A dermoscopy image of a single skin lesion.
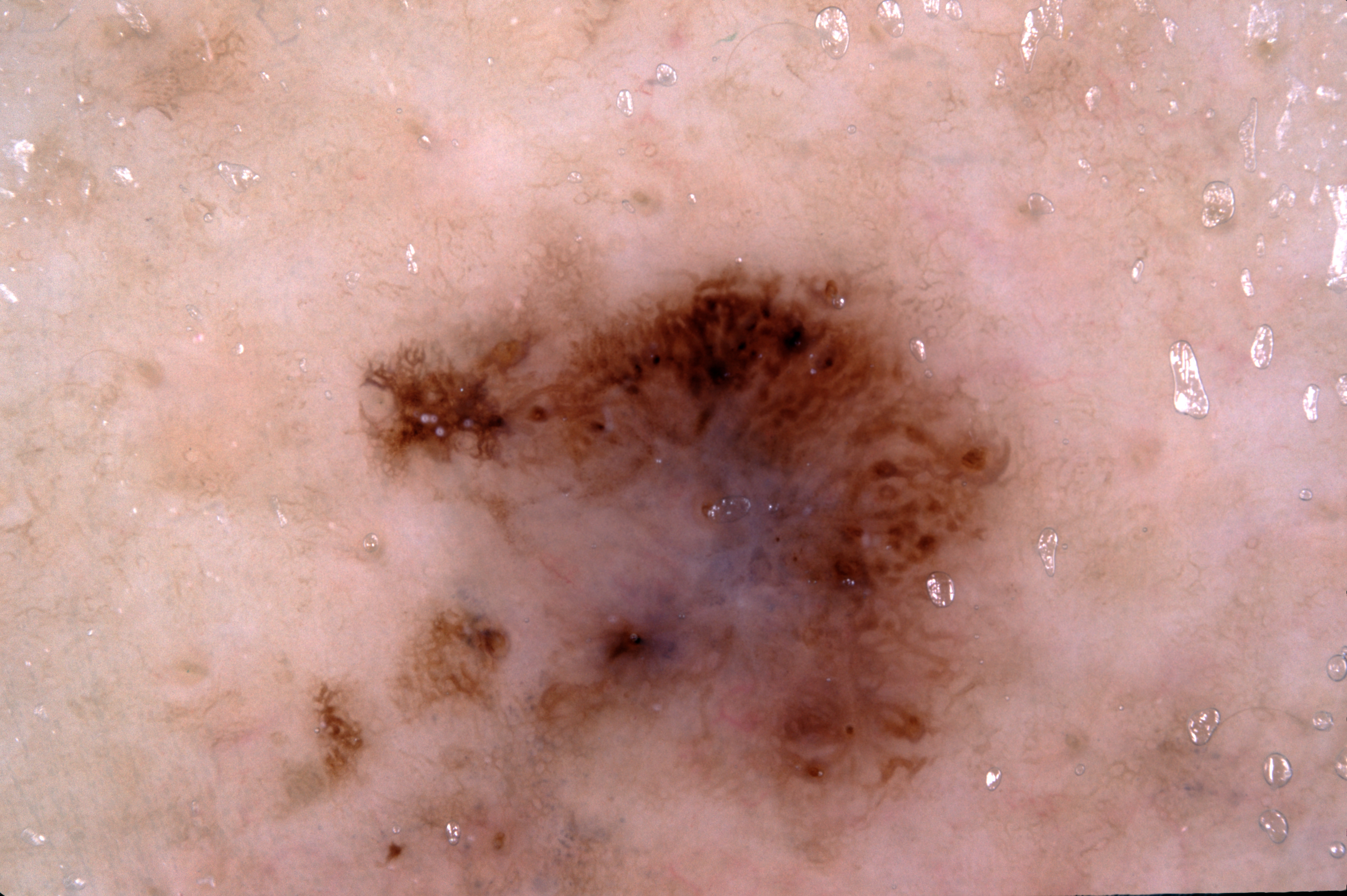With coordinates (x1, y1, x2, y2), the lesion occupies the region <box>271, 219, 1118, 895</box>. The lesion takes up a large portion of the image. Dermoscopic examination shows pigment network. Histopathology confirmed a melanoma.